A male subject, in their 60s. Dermoscopy of a skin lesion — 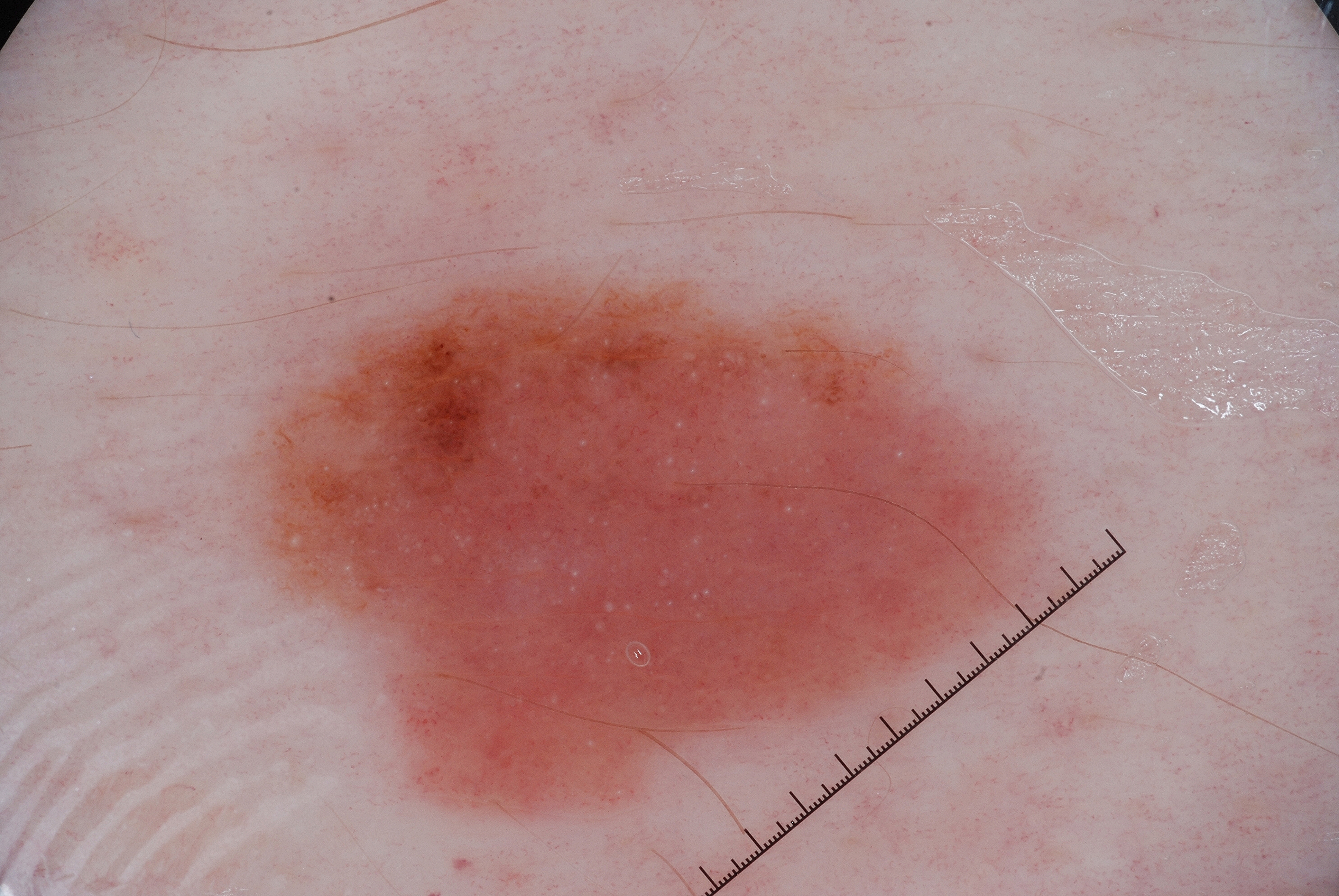{
  "lesion_extent": {
    "approx_field_fraction_pct": 30
  },
  "lesion_location": {
    "bbox_xyxy": [
      225,
      242,
      1073,
      831
    ]
  },
  "dermoscopic_features": {
    "present": [
      "milia-like cysts"
    ],
    "absent": [
      "streaks",
      "negative network",
      "pigment network"
    ]
  },
  "diagnosis": {
    "name": "melanoma",
    "malignancy": "malignant",
    "lineage": "melanocytic",
    "provenance": "histopathology"
  }
}